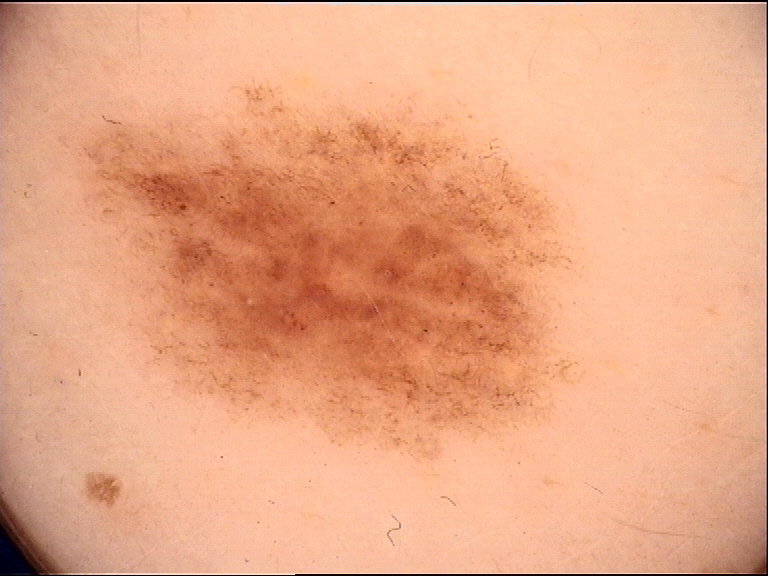| field | value |
|---|---|
| diagnostic label | dysplastic junctional nevus (expert consensus) |